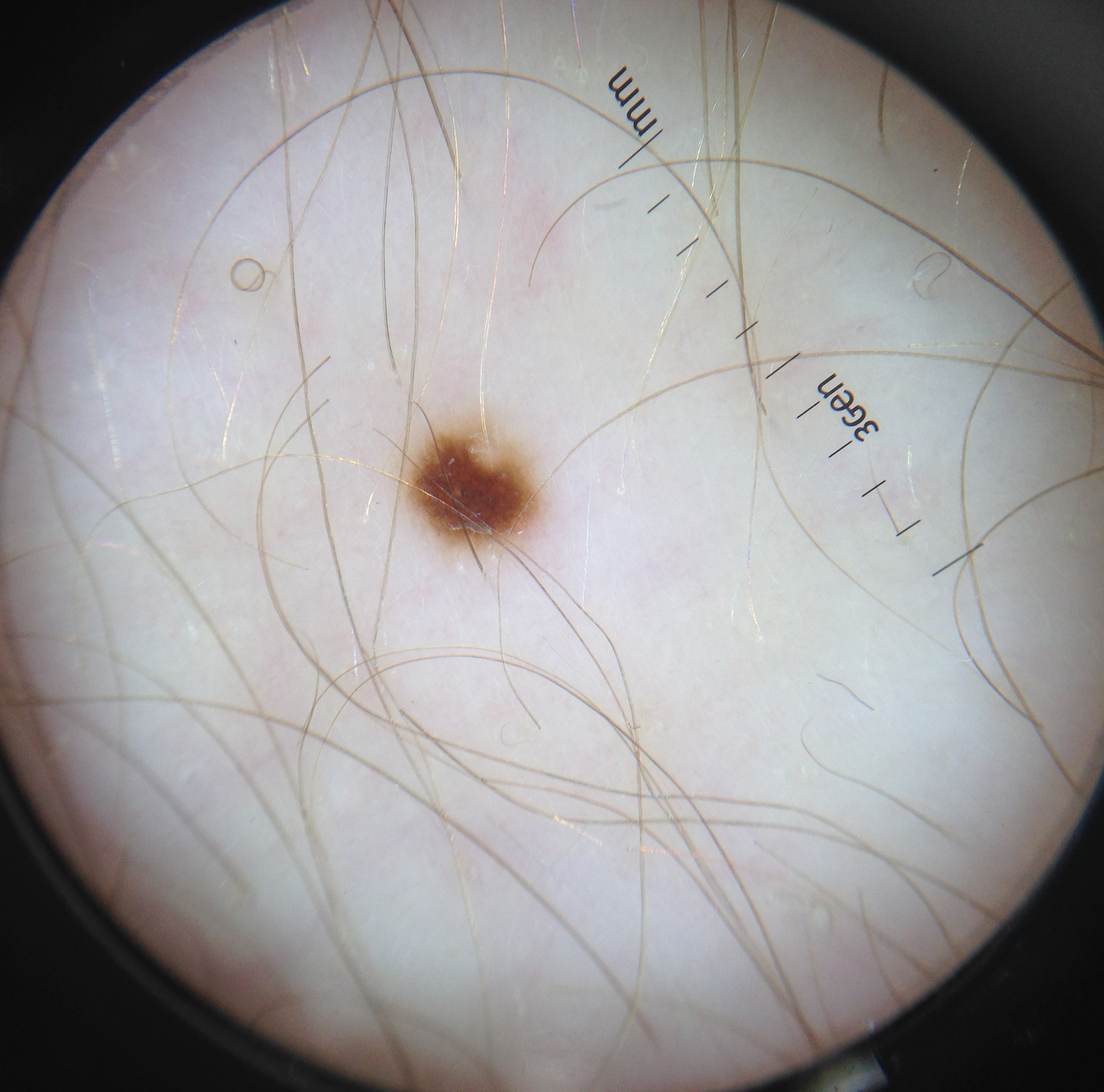The morphology is that of a banal lesion.
Classified as a junctional nevus.